Located on the leg · the photo was captured at a distance · female patient, age 60–69: 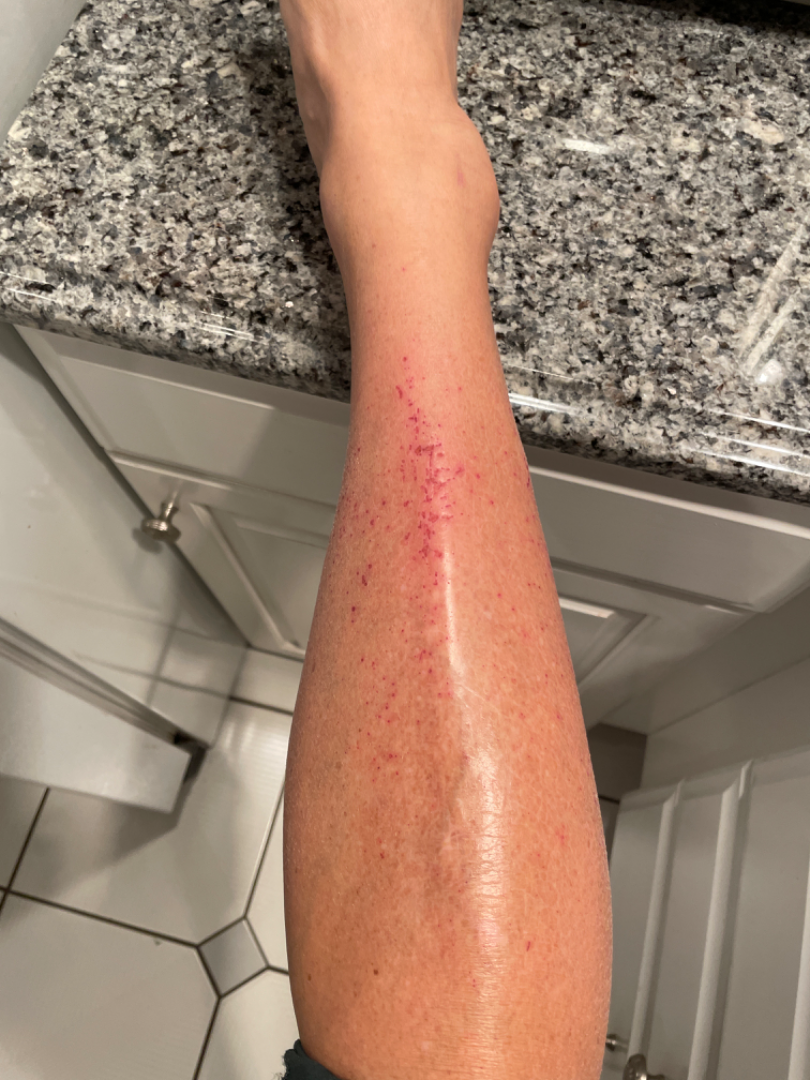skin tone=Fitzpatrick III; human graders estimated 3 on the Monk Skin Tone
symptoms=bothersome appearance and enlargement
symptom duration=less than one week
lesion texture=raised or bumpy
dermatologist impression=most consistent with Eczema; also consider Xerosis